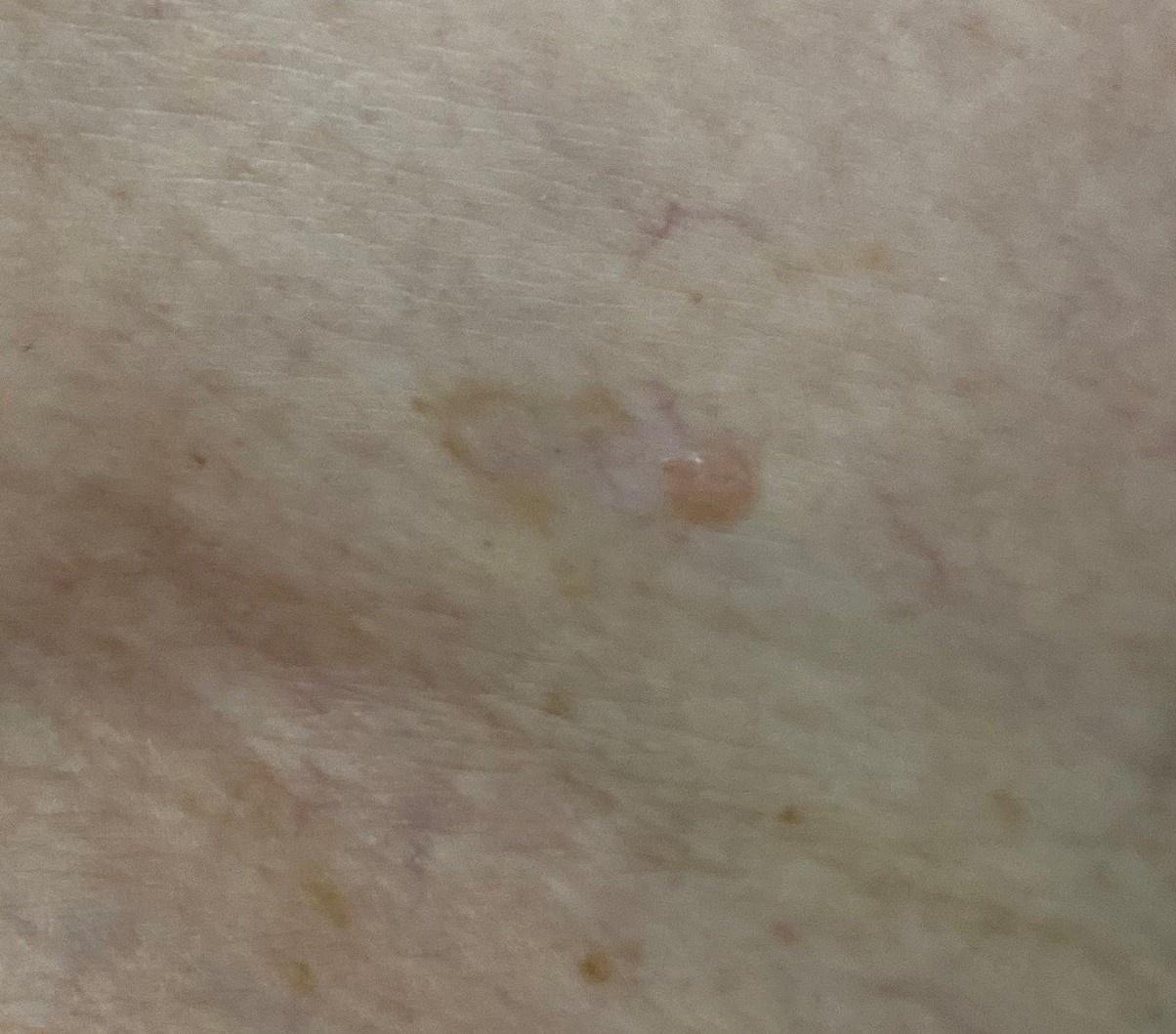Findings:
A female subject aged around 55.
Diagnosis:
Histopathologically confirmed as a nevus.